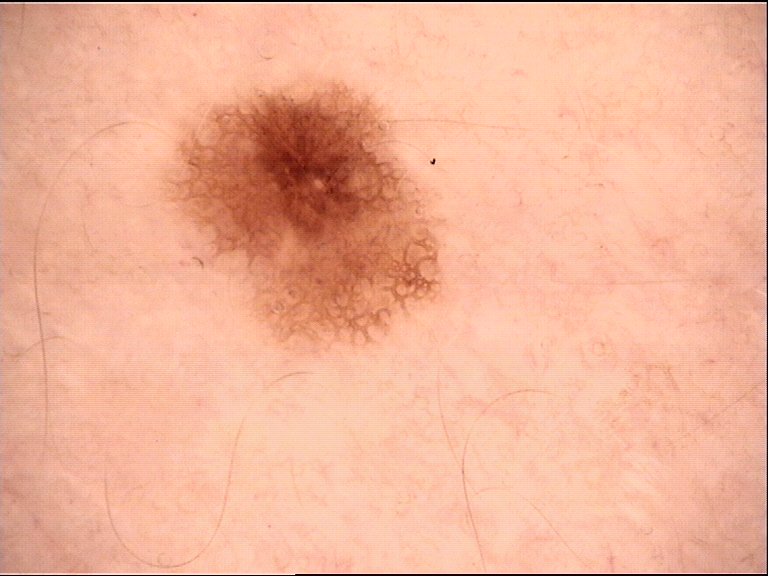<lesion>
<diagnosis>
<name>dysplastic junctional nevus</name>
<code>jd</code>
<malignancy>benign</malignancy>
<super_class>melanocytic</super_class>
<confirmation>expert consensus</confirmation>
</diagnosis>
</lesion>